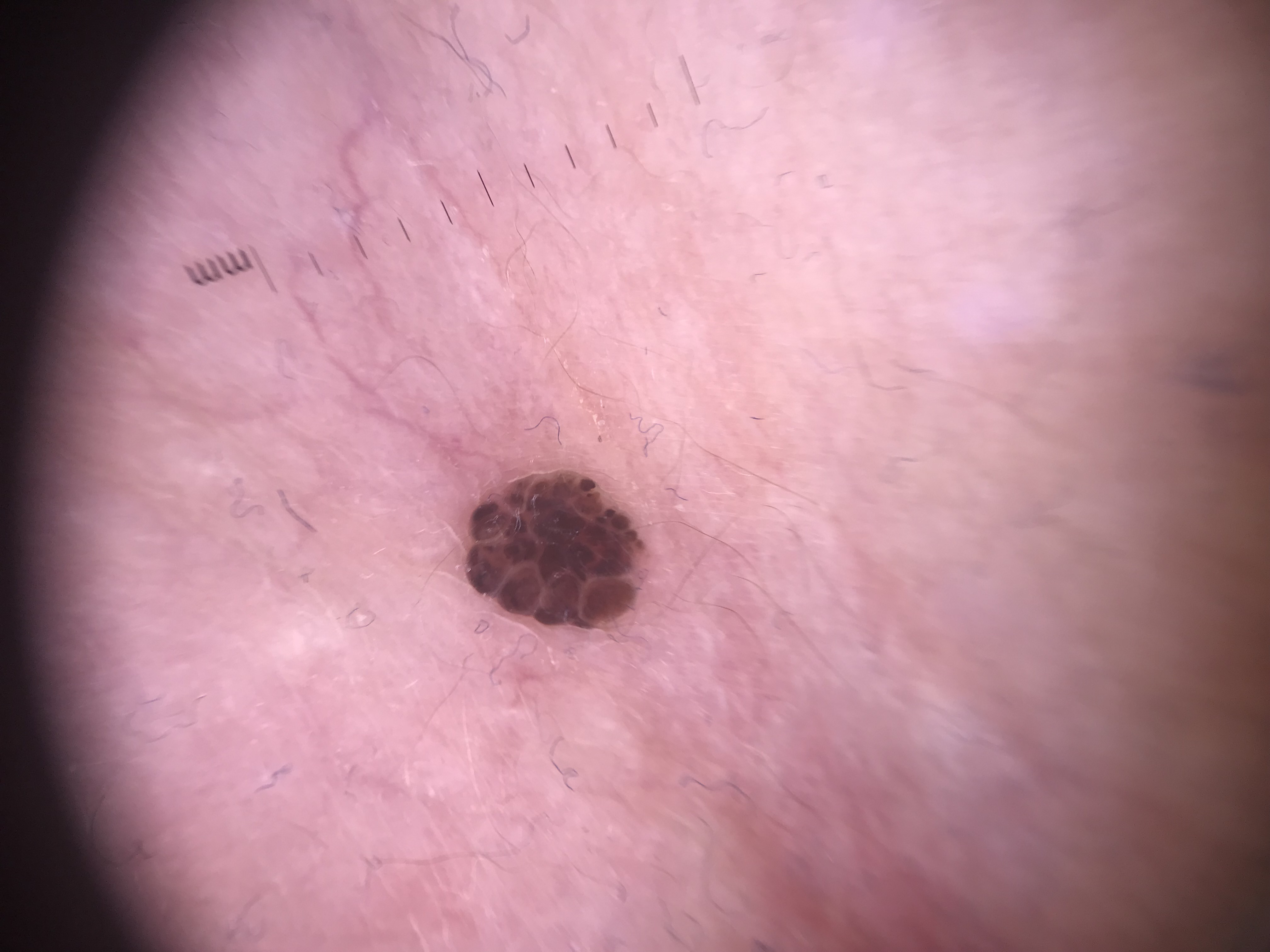Summary: A skin lesion imaged with a dermatoscope. The morphology is that of a banal lesion. Conclusion: Consistent with a compound nevus.